The affected area is the leg. The photo was captured at an angle: 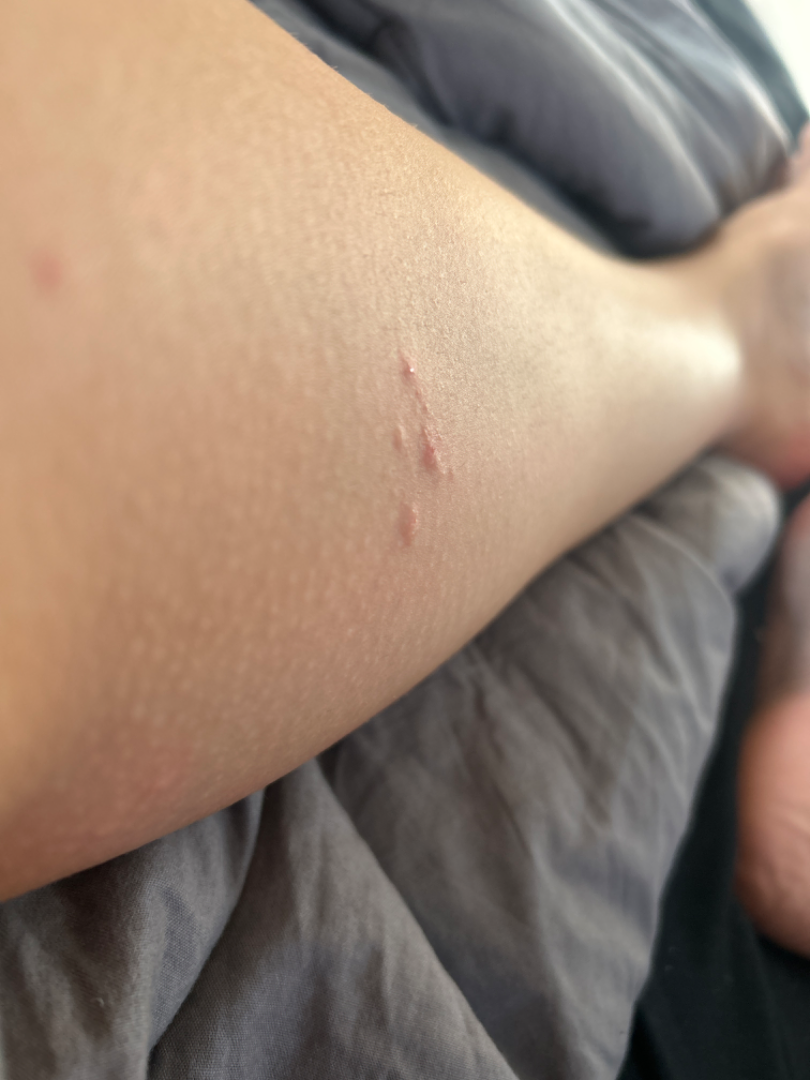{
  "systemic_symptoms": "none reported",
  "symptoms": "itching",
  "patient_category": "a rash",
  "duration": "less than one week",
  "differential": {
    "tied_lead": [
      "Insect Bite",
      "Allergic Contact Dermatitis",
      "Herpes Simplex"
    ]
  }
}